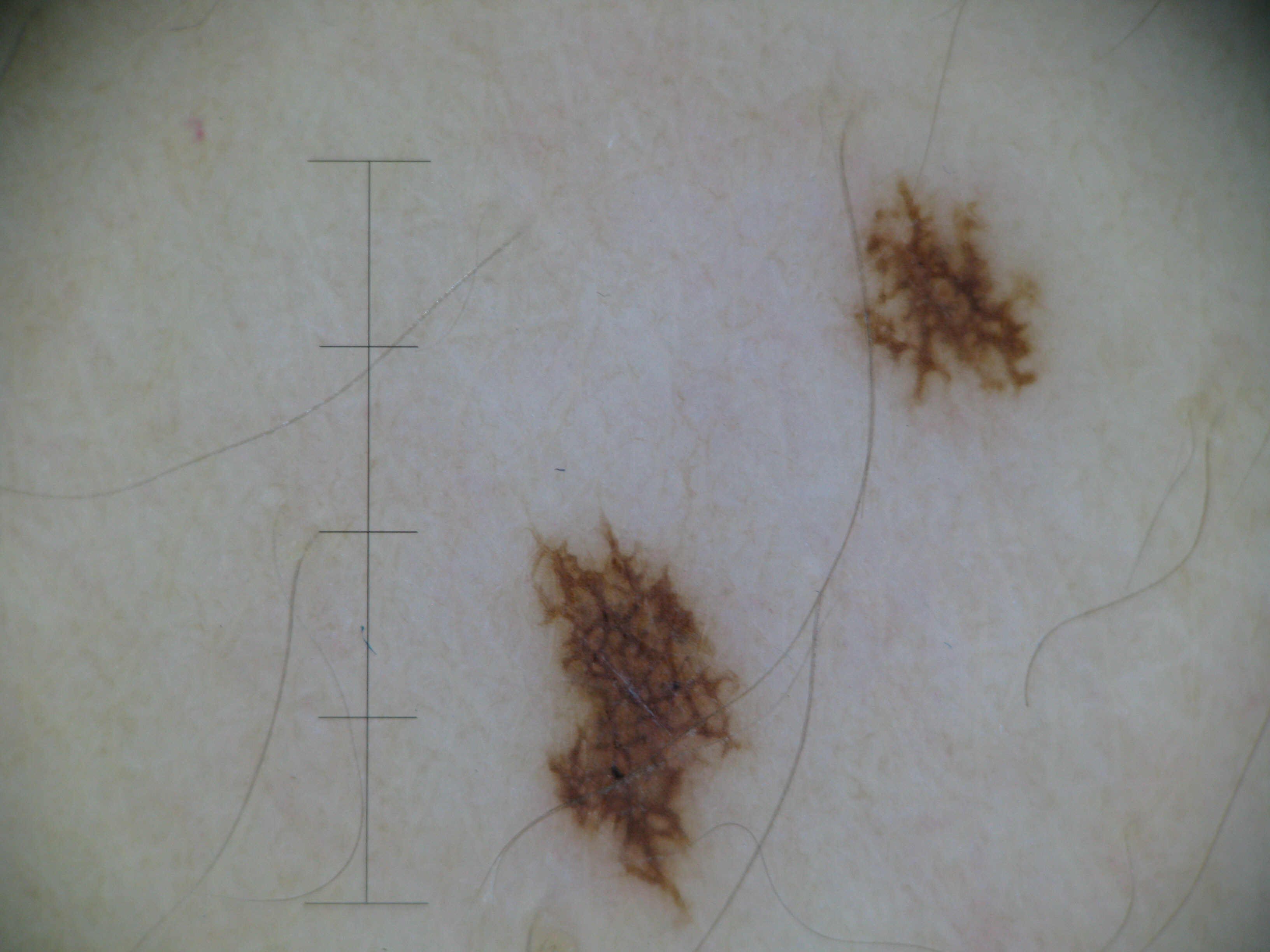<lesion>
<diagnosis>
<name>acral junctional nevus</name>
<code>ajb</code>
<malignancy>benign</malignancy>
<super_class>melanocytic</super_class>
<confirmation>expert consensus</confirmation>
</diagnosis>
</lesion>